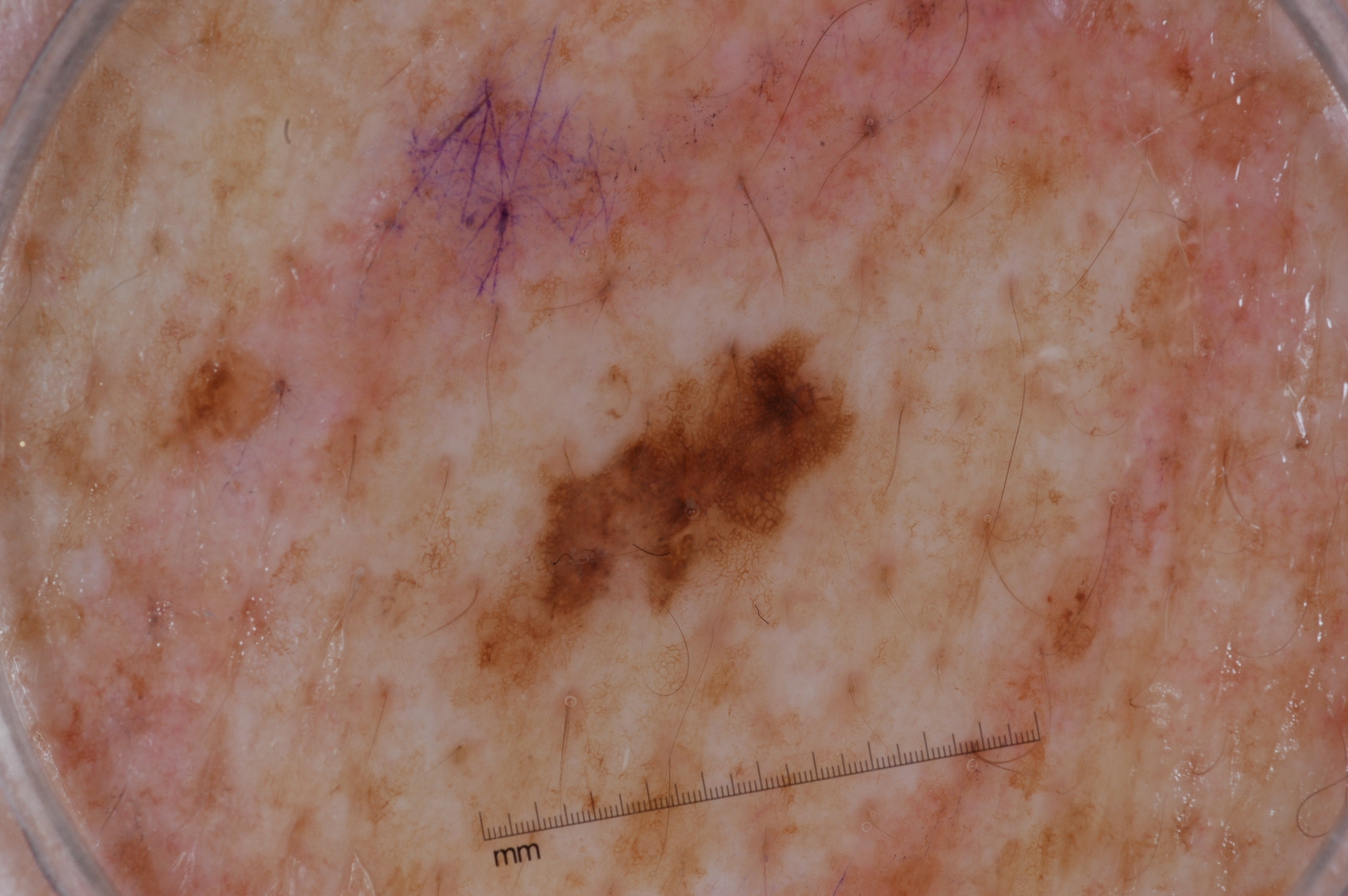| feature | finding |
|---|---|
| modality | dermatoscopic image of a skin lesion |
| dermoscopic findings | pigment network |
| lesion bbox | <box>537, 350, 842, 623</box> |
| lesion extent | small |
| diagnostic label | a melanocytic nevus, a benign lesion |